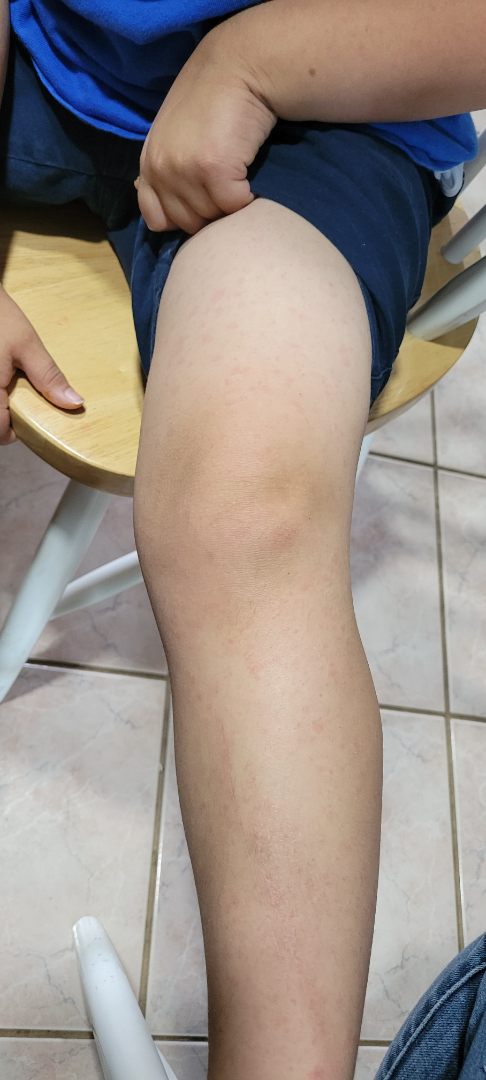The skin condition could not be confidently assessed from this image.
The photo was captured at a distance.
The affected area is the arm and leg.